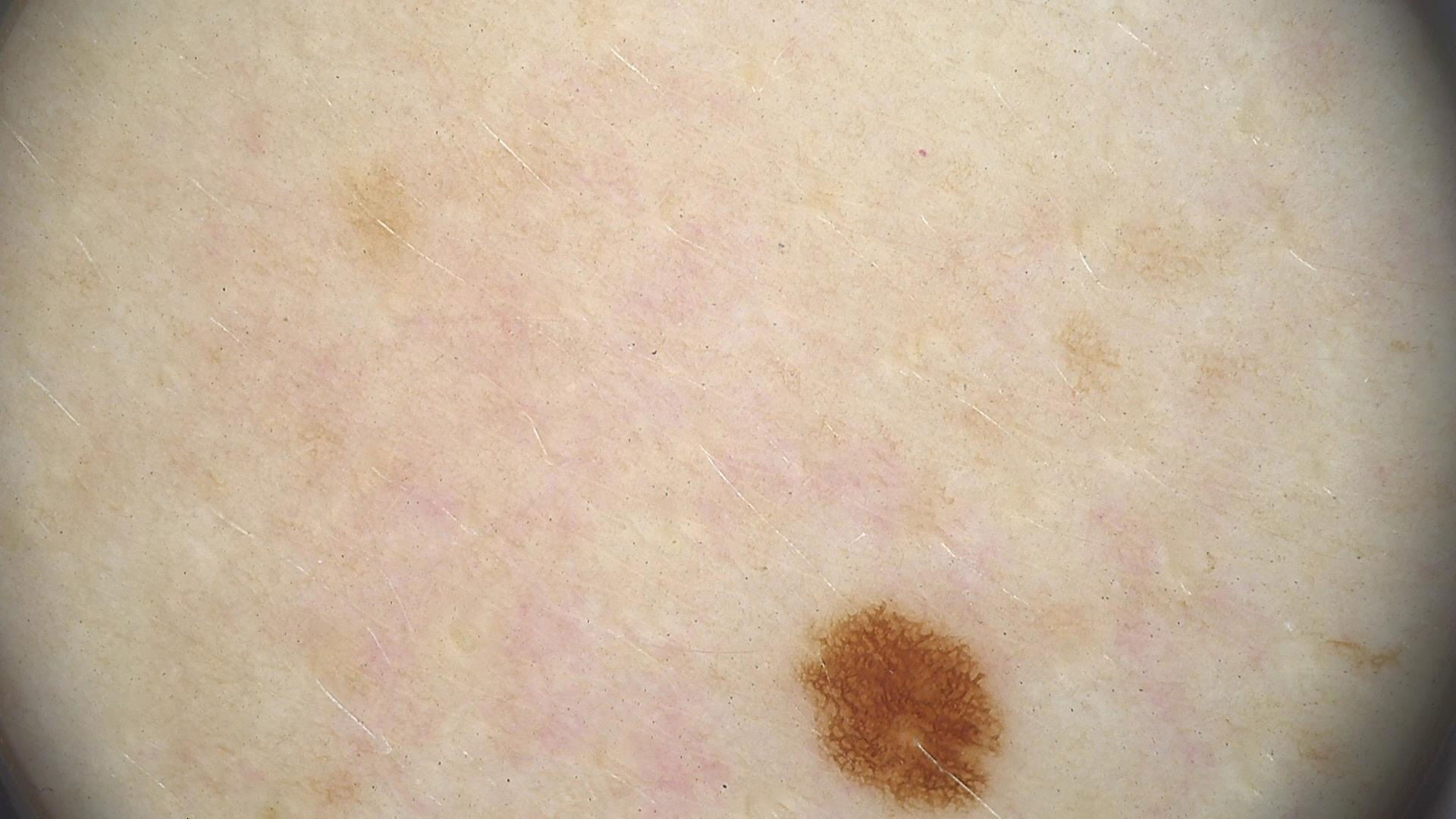Summary: A dermoscopy image of a single skin lesion. Impression: Labeled as a junctional nevus.